The patient is 18–29, female; this image was taken at an angle; the affected area is the back of the hand: 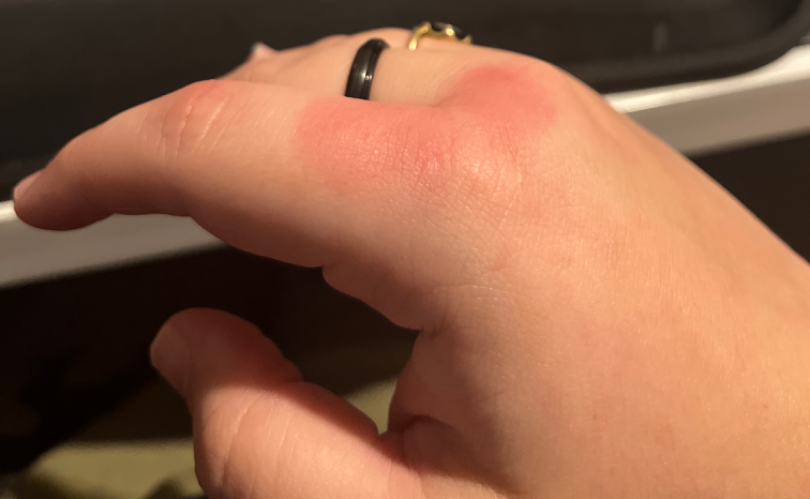Urticaria (possible); Insect Bite (possible); Cellulitis (unlikely).